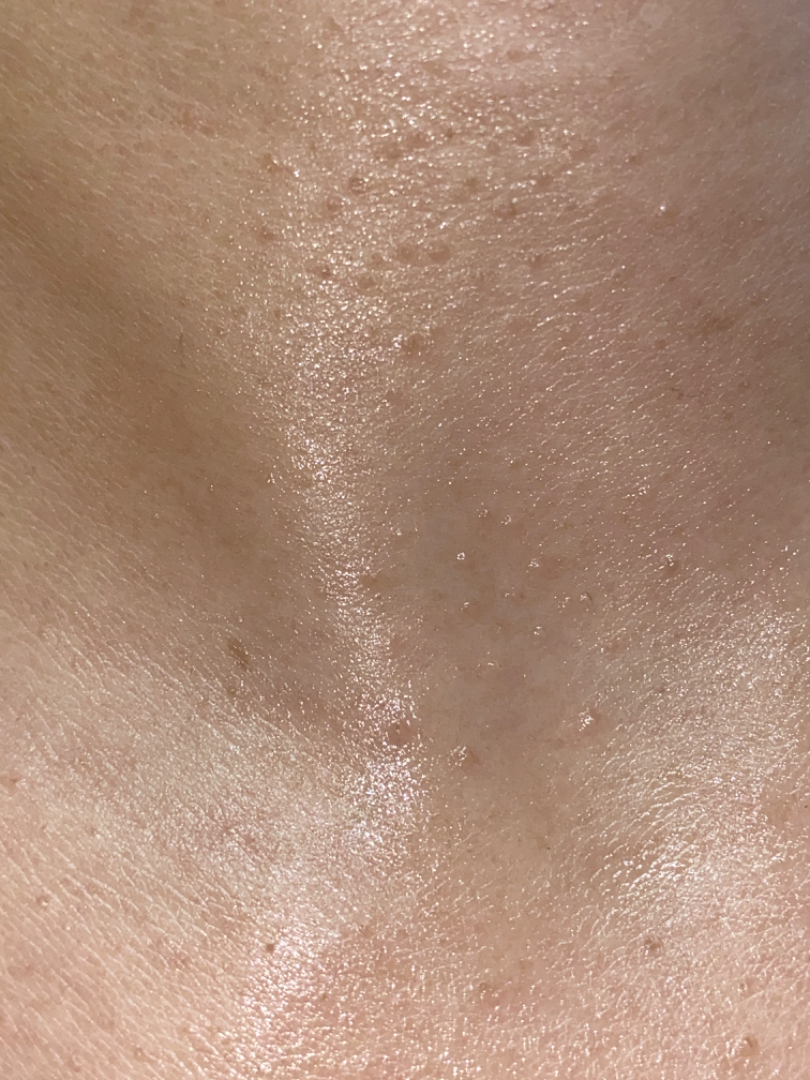assessment: unable to determine
shot_type: close-up
body_site: head or neck